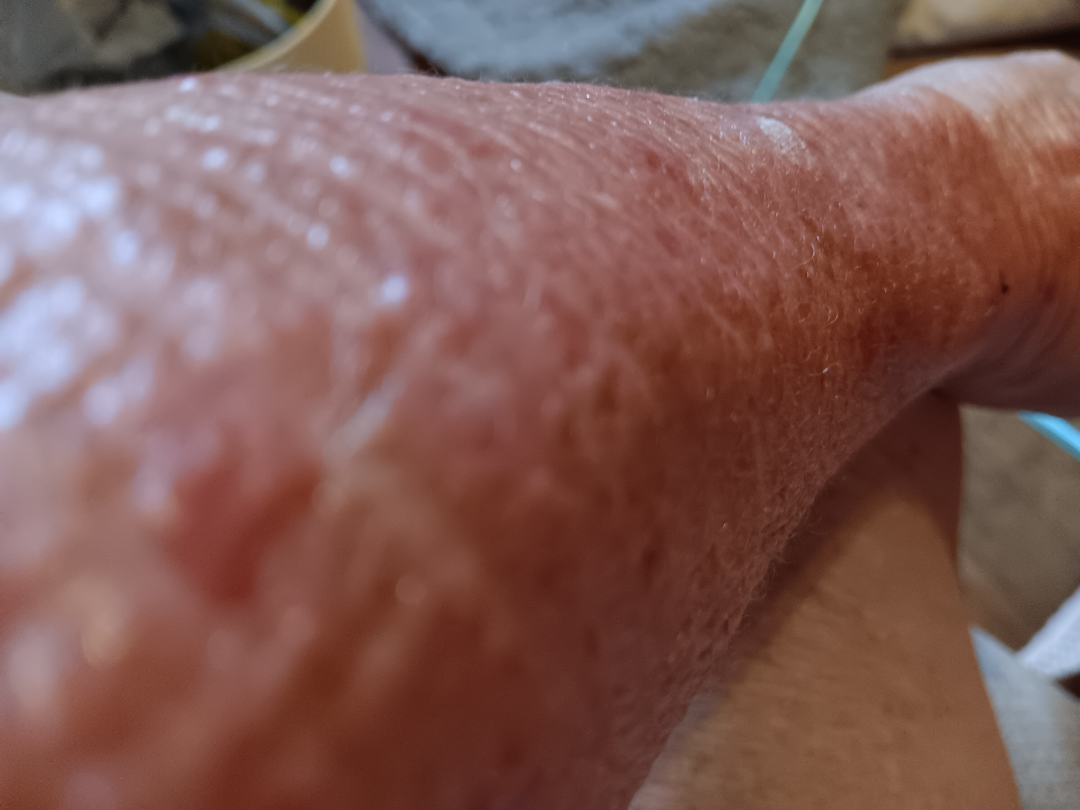On photographic review by a dermatologist: most consistent with SCC/SCCIS.